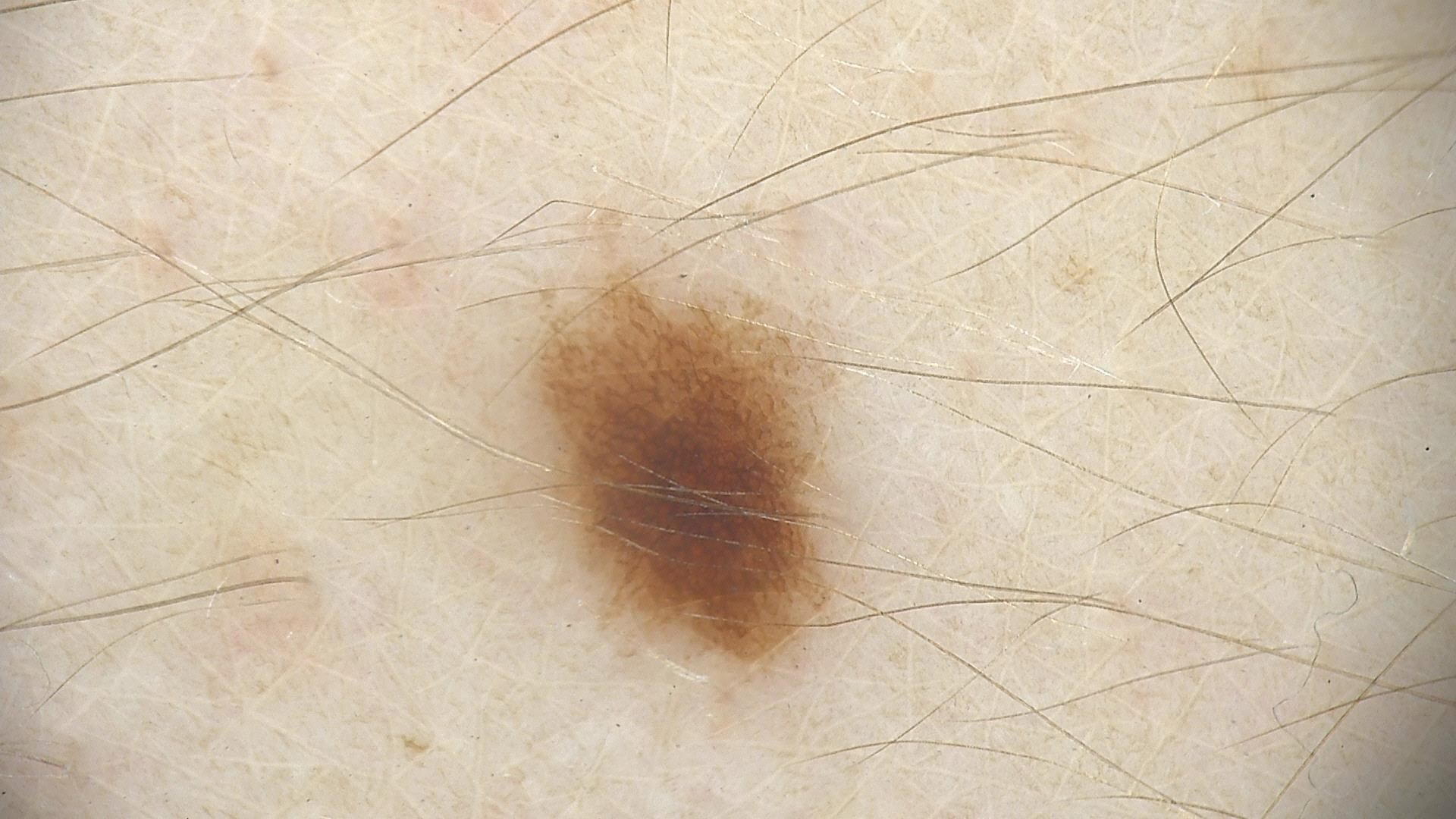Impression: Consistent with a benign lesion — a dysplastic junctional nevus.